A clinical photograph of a skin lesion — 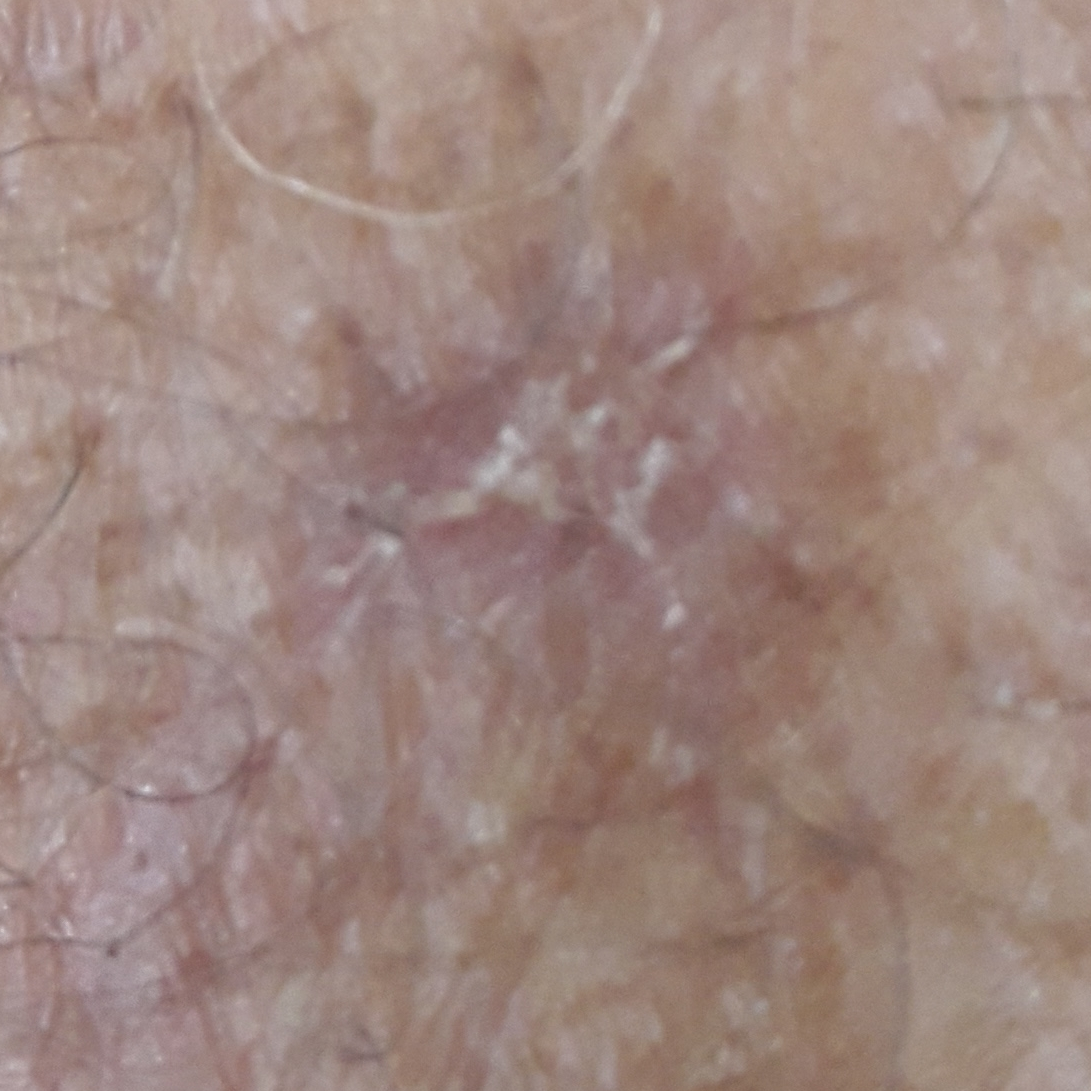anatomic site — an arm | symptoms — itching | diagnostic label — actinic keratosis (clinical consensus).